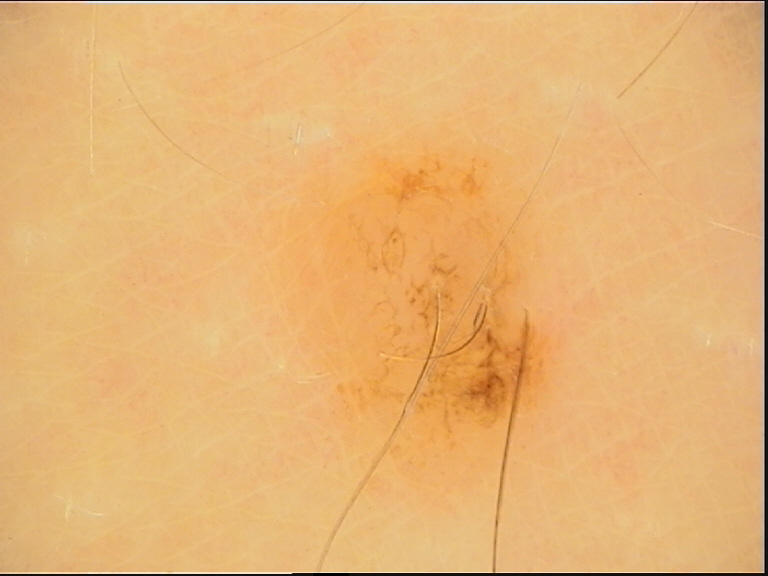imaging: dermatoscopy, classification: banal, diagnostic label: junctional nevus (expert consensus).